Dermoscopy of a skin lesion.
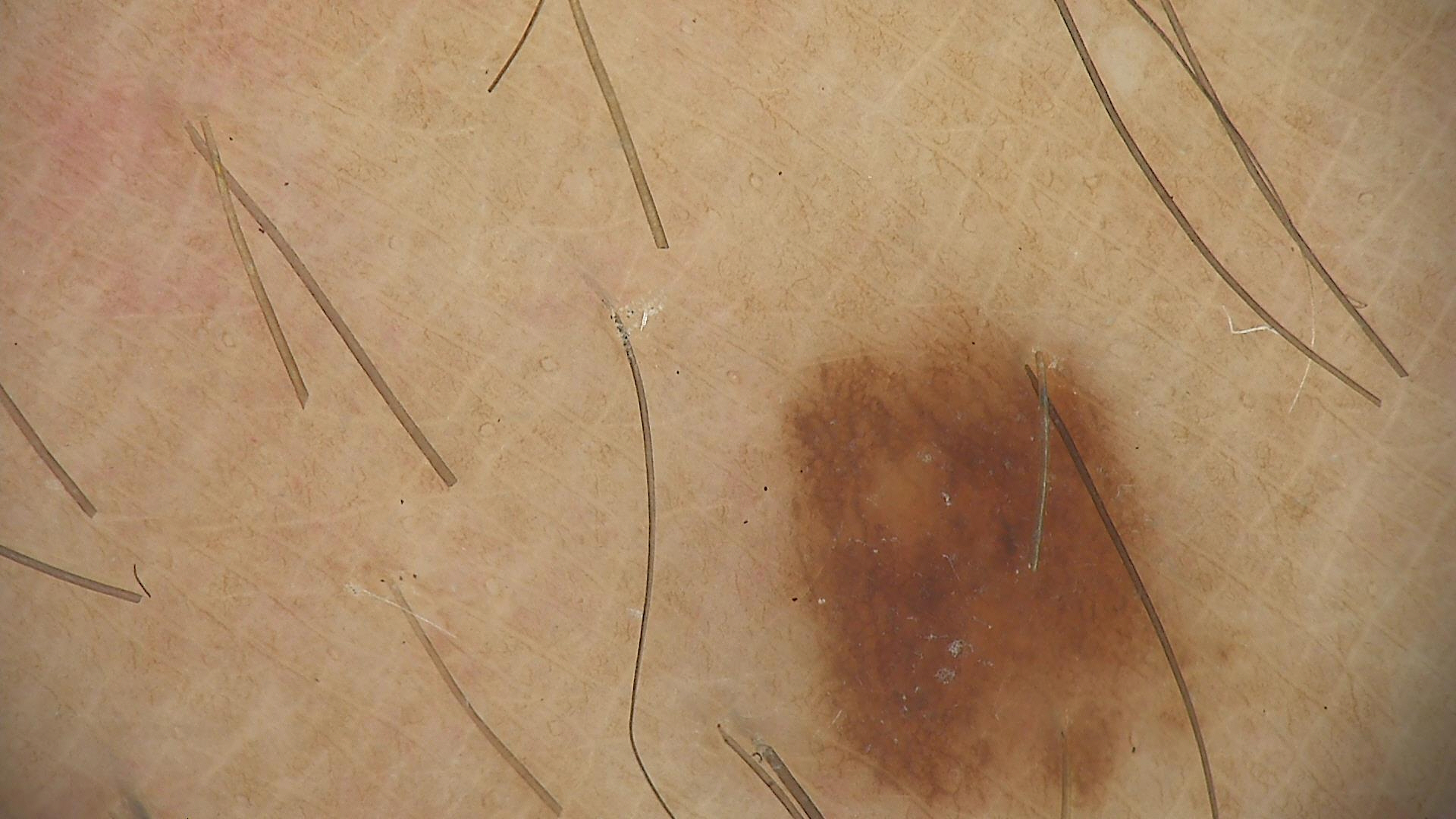| key | value |
|---|---|
| assessment | dysplastic junctional nevus (expert consensus) |